The arm is involved. Female patient, age 30–39. Close-up view:
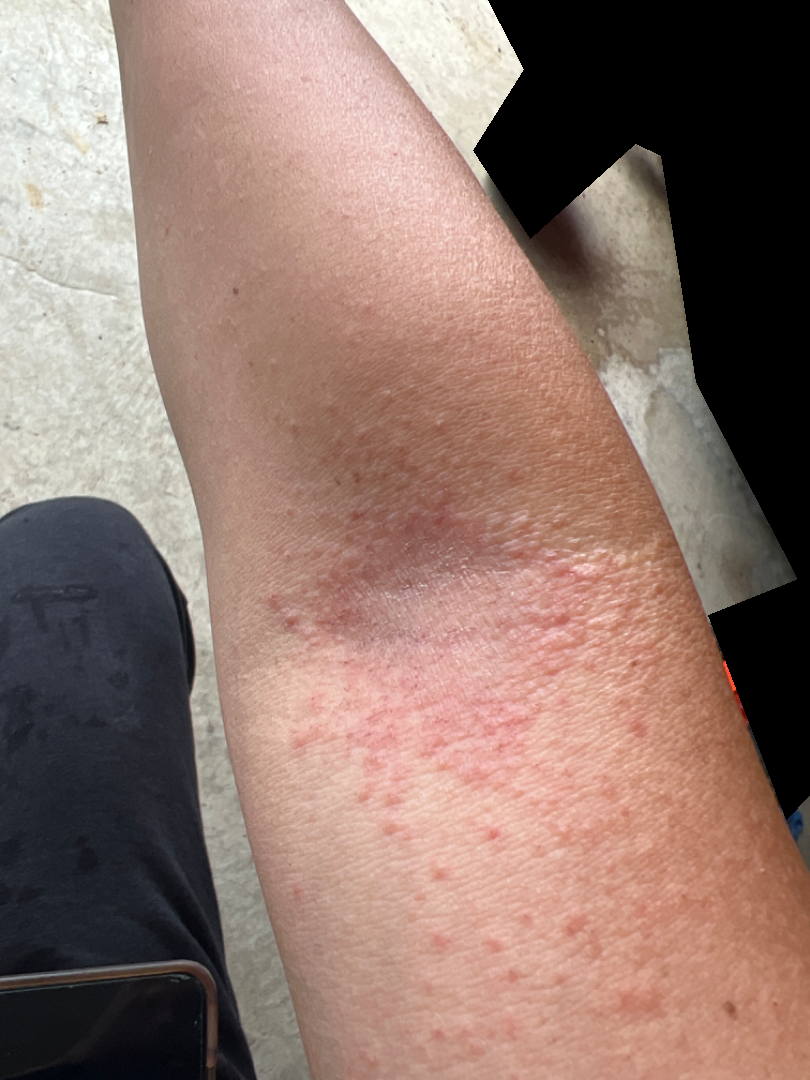Findings:
• impression: favoring Eczema; the differential also includes Allergic Contact Dermatitis; less probable is Tinea